A dermoscopic photograph of a skin lesion.
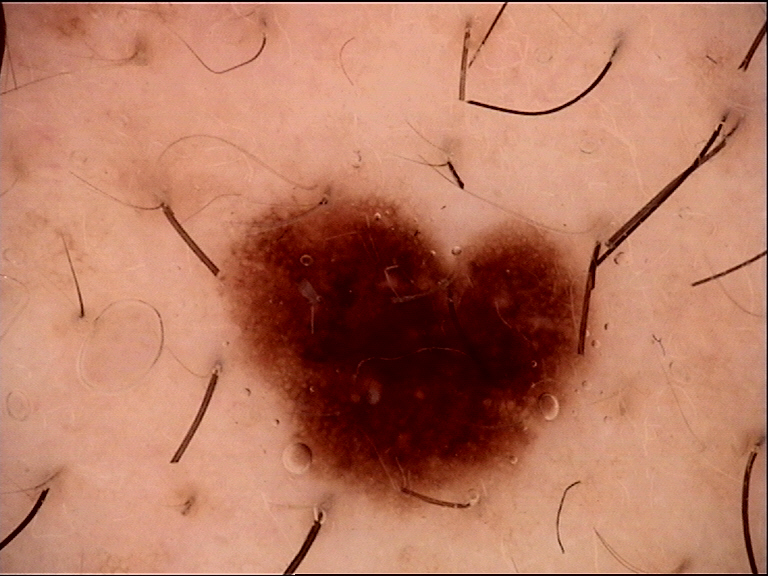Q: What was the diagnostic impression?
A: dysplastic junctional nevus (expert consensus)